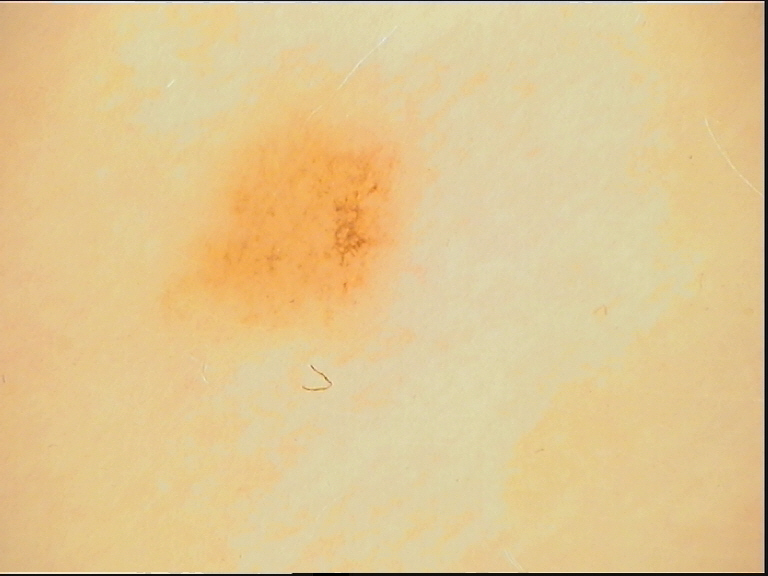Conclusion: The diagnostic label was a junctional nevus.